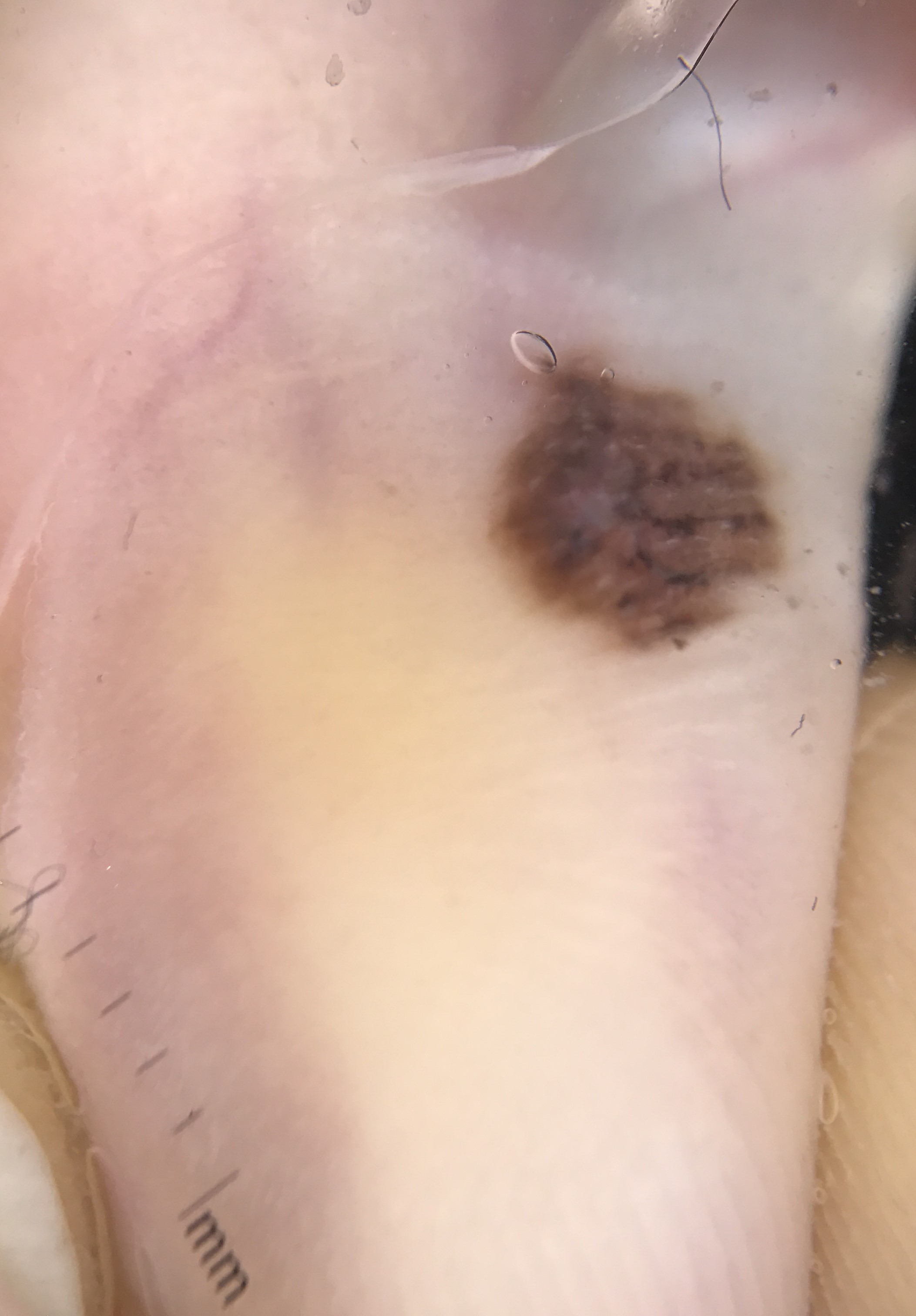| feature | finding |
|---|---|
| image type | dermatoscopy |
| class | acral dysplastic compound nevus (expert consensus) |